A skin lesion imaged with a dermatoscope.
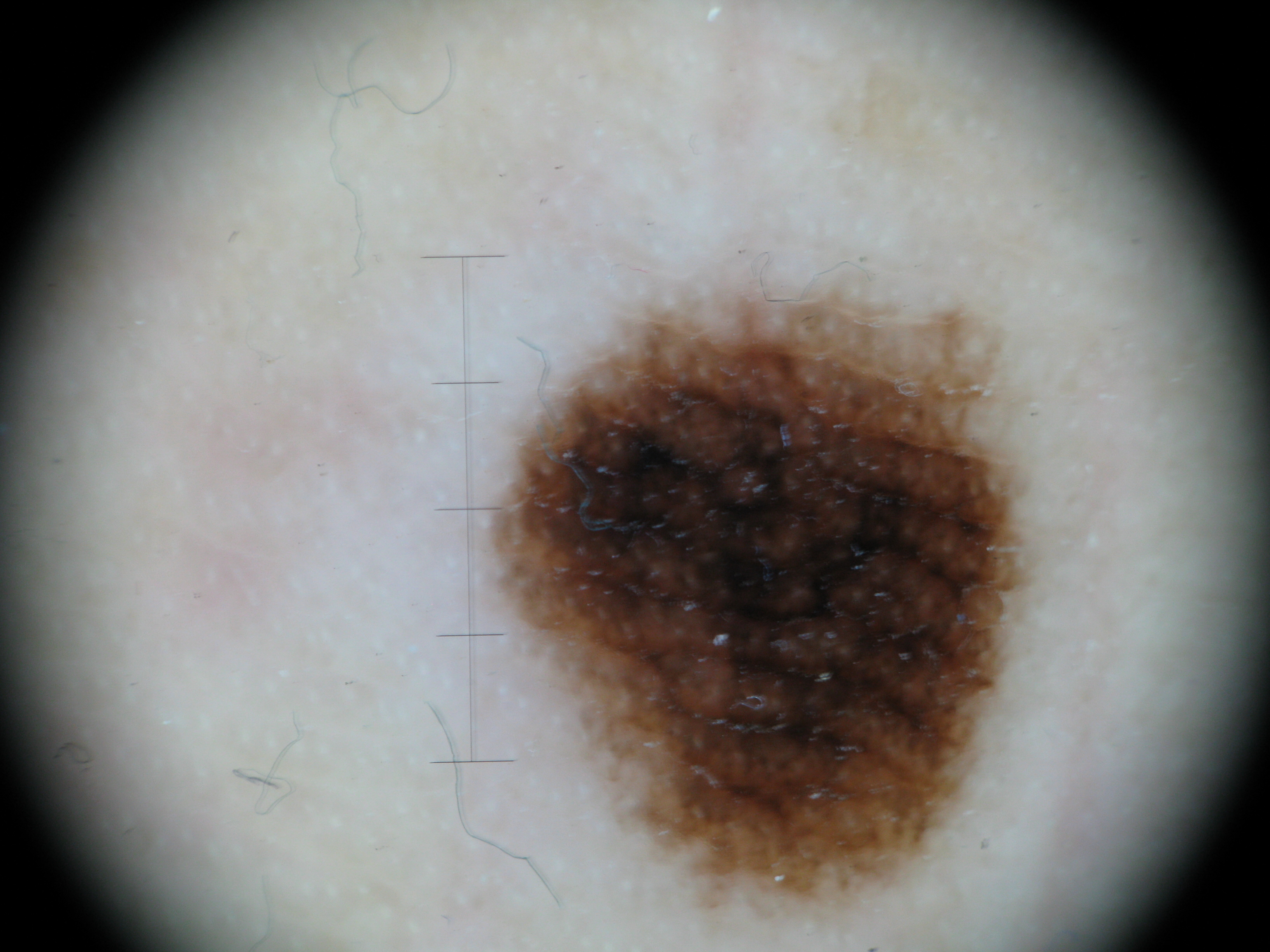Conclusion:
The diagnostic label was a banal lesion — an acral junctional nevus.